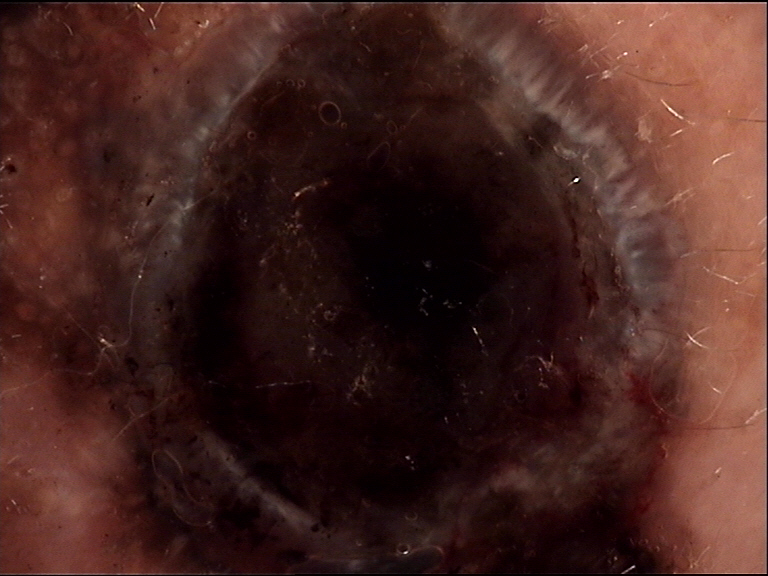{"image": "dermoscopy", "diagnosis": {"name": "lentigo maligna melanoma", "code": "lmm", "malignancy": "malignant", "super_class": "melanocytic", "confirmation": "histopathology"}}